A dermoscopic view of a skin lesion · a female subject roughly 35 years of age:
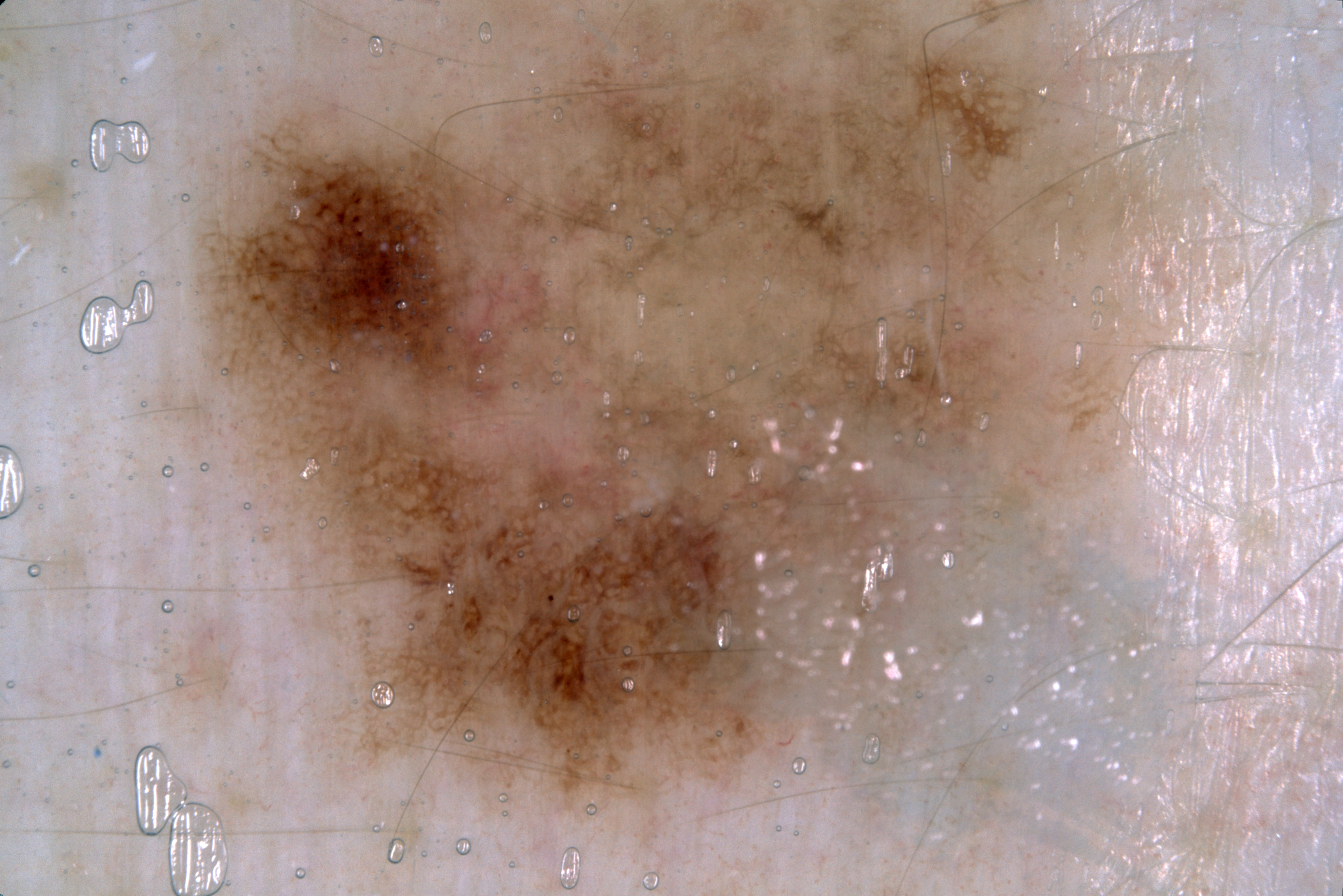With coordinates (x1, y1, x2, y2), the lesion is bounded by 194, 0, 1158, 816.
Dermoscopy demonstrates pigment network, with no negative network, milia-like cysts, or streaks.
The lesion covers approximately 48% of the dermoscopic field.
The lesion is clipped by the edge of the image.
Consistent with a melanocytic nevus, a benign skin lesion.